Symptoms reported: burning and itching. Skin tone: non-clinician graders estimated 2 on the Monk Skin Tone. The condition has been present for less than one week. An image taken at an angle. The affected area is the arm and head or neck. The contributor reports the lesion is raised or bumpy. The subject is 60–69, female.
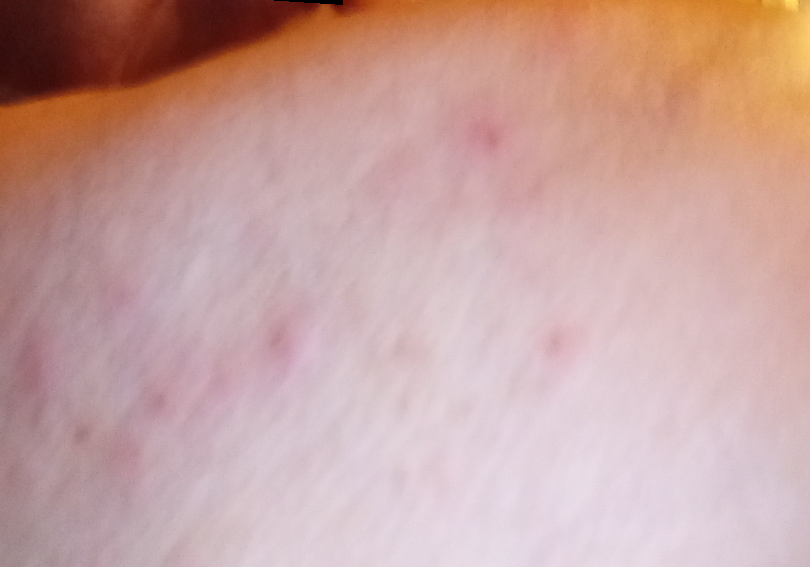assessment: could not be assessed